The patient notes the lesion is rough or flaky. The patient notes the condition has been present for more than one year. This image was taken at an angle. The lesion involves the top or side of the foot, leg and palm. Symptoms reported: itching, darkening, enlargement, pain and bothersome appearance — 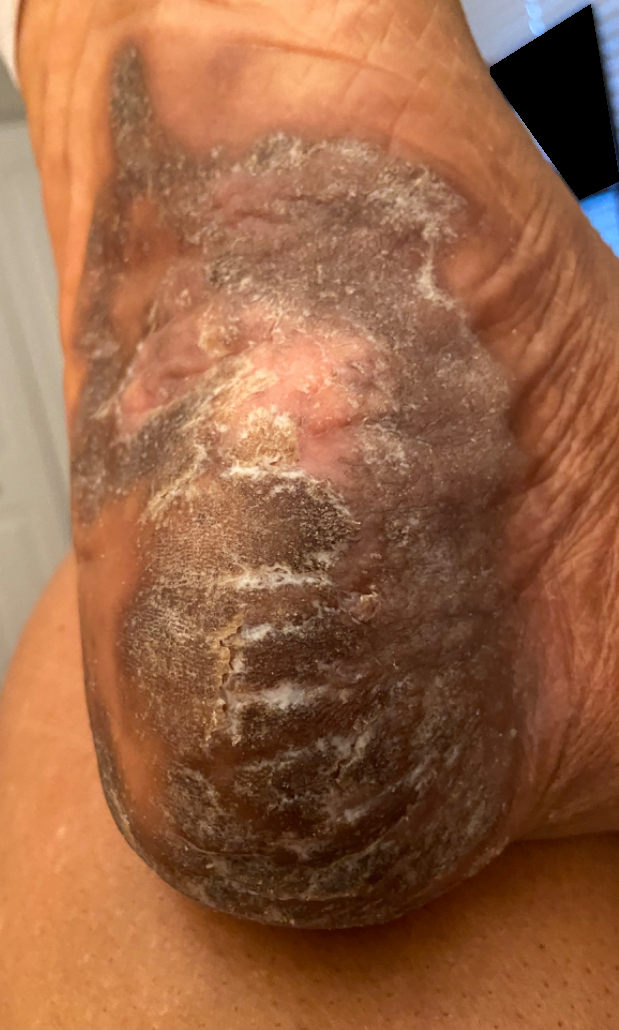{
  "assessment": "indeterminate from the photograph"
}